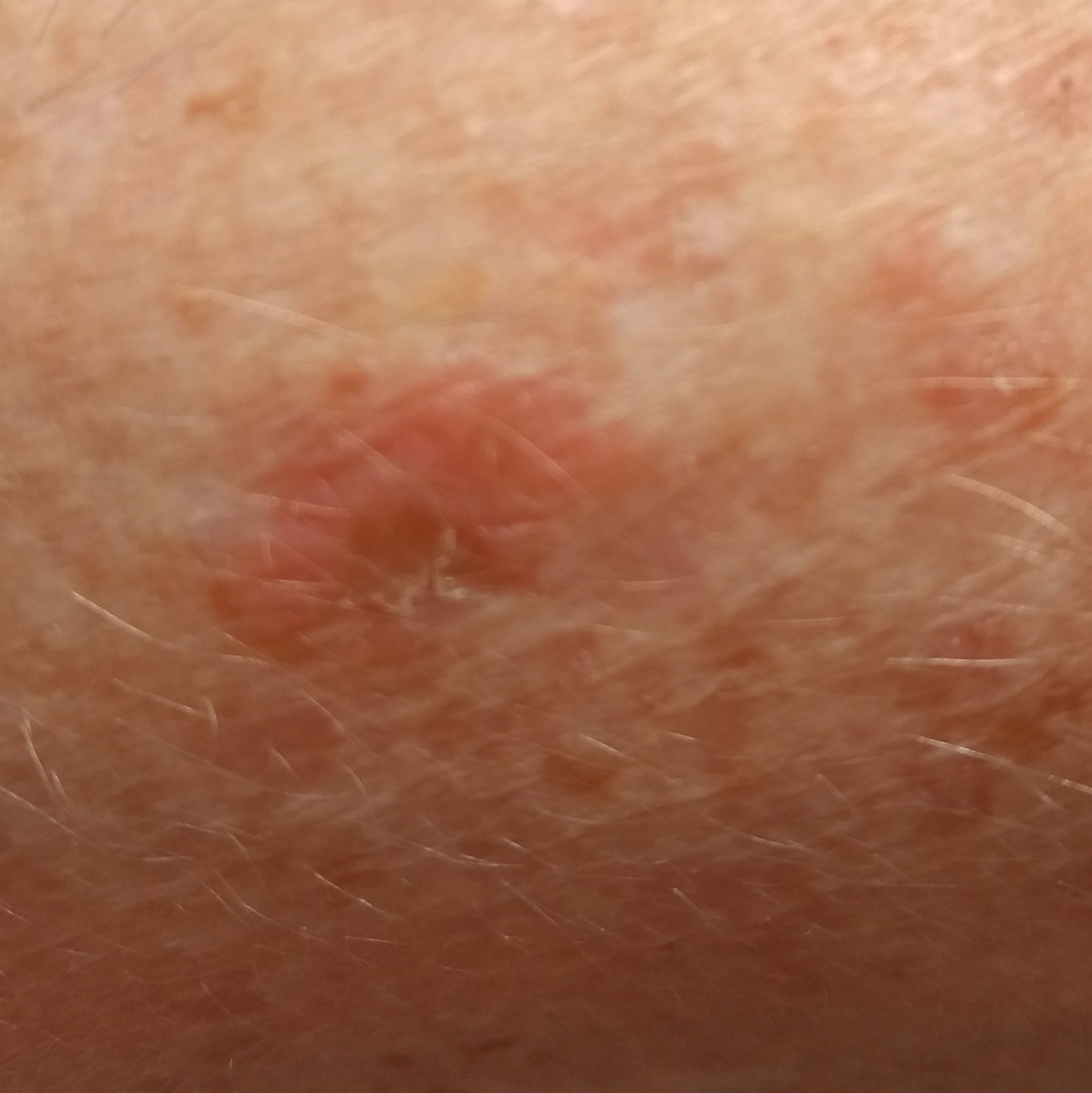modality — clinical photo | subject — 60 years old | location — an arm | patient-reported symptoms — no pain, no growth | impression — actinic keratosis (clinical consensus).